The photograph is a close-up of the affected area — 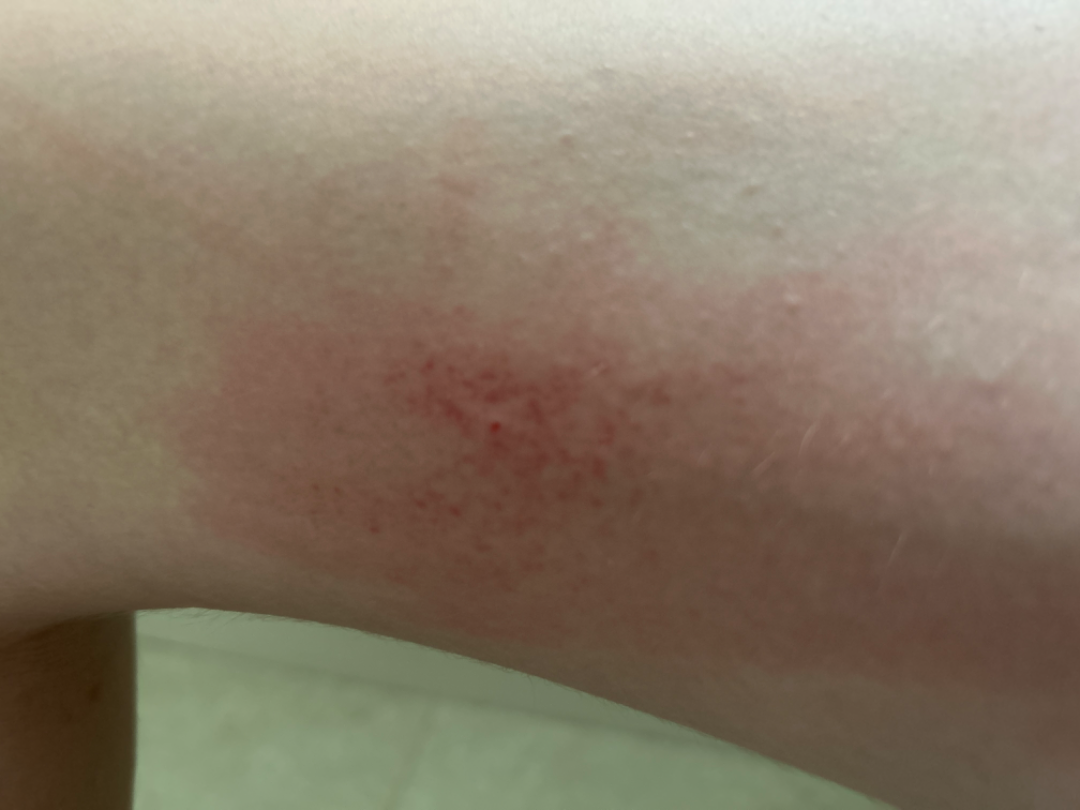assessment: ungradable on photographic review